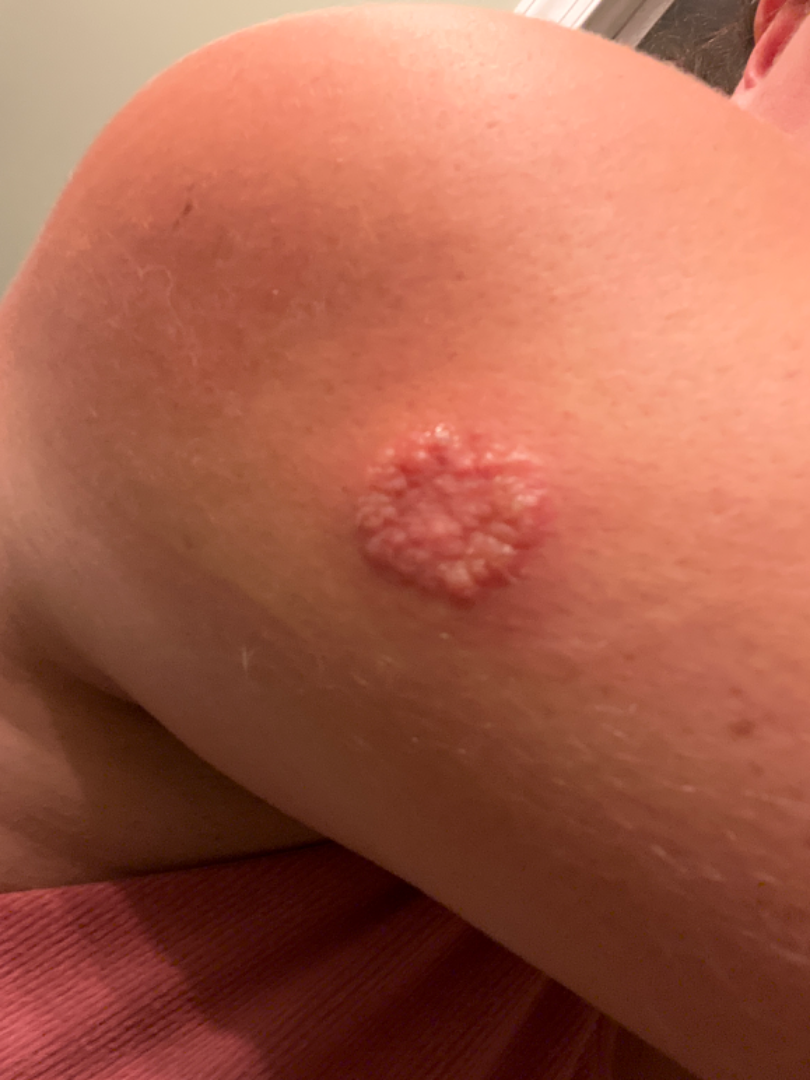The skin findings could not be characterized from the image.